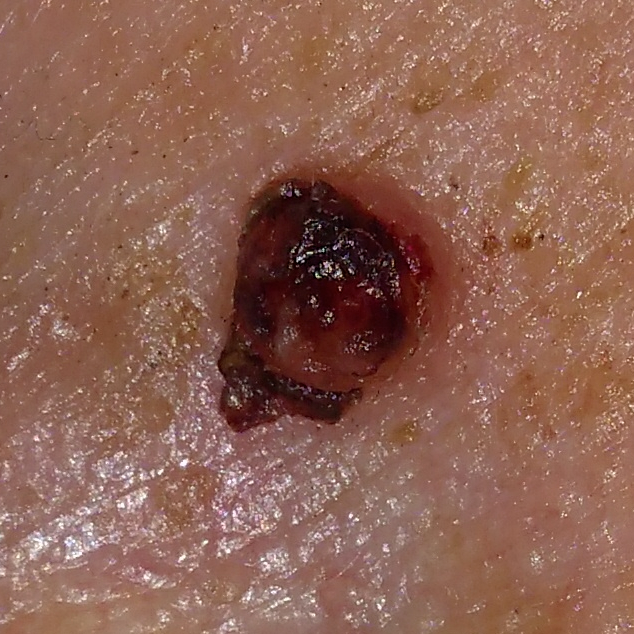{
  "patient": {
    "age": 30,
    "gender": "female"
  },
  "image": "clinical photo",
  "lesion_location": "the nose",
  "symptoms": {
    "present": [
      "bleeding",
      "pain",
      "elevation",
      "itching"
    ]
  },
  "diagnosis": {
    "name": "basal cell carcinoma",
    "code": "BCC",
    "malignancy": "malignant",
    "confirmation": "histopathology"
  }
}